The affected area is the head or neck, the photograph was taken at an angle:
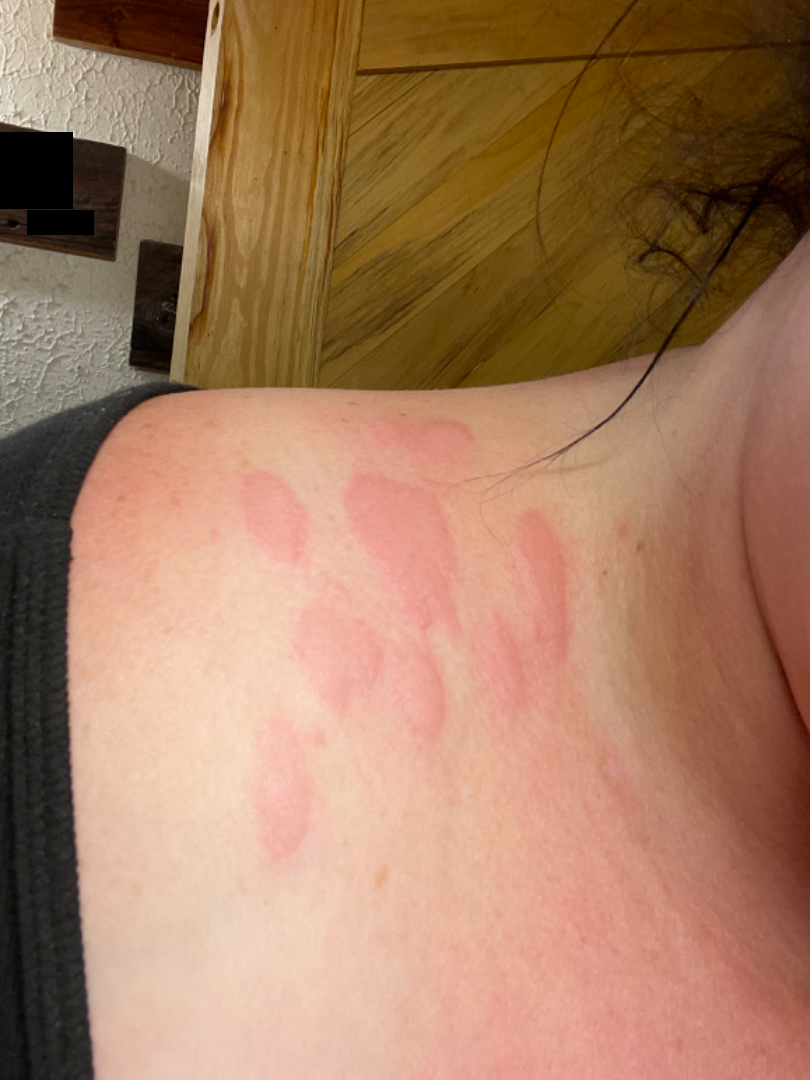Q: What conditions are considered?
A: the impression is Urticaria